A dermoscopy image of a single skin lesion; a male subject about 30 years old:
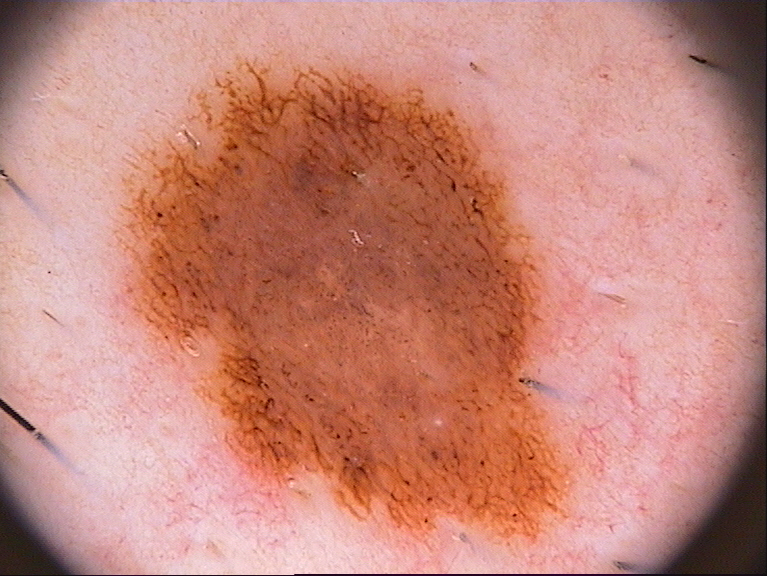lesion_location:
  bbox_xyxy:
    - 123
    - 51
    - 573
    - 536
lesion_extent:
  approx_field_fraction_pct: 36
dermoscopic_features:
  present:
    - globules
    - pigment network
  absent:
    - streaks
    - negative network
    - milia-like cysts
diagnosis:
  name: melanocytic nevus
  malignancy: benign
  lineage: melanocytic
  provenance: clinical